Located on the arm · the subject is female · the patient indicates the lesion is raised or bumpy · Fitzpatrick phototype IV · a close-up photograph · the patient described the issue as a rash · symptoms reported: pain, enlargement, bothersome appearance, darkening, itching and burning · present for one to three months · the patient also reports fever, fatigue and joint pain — 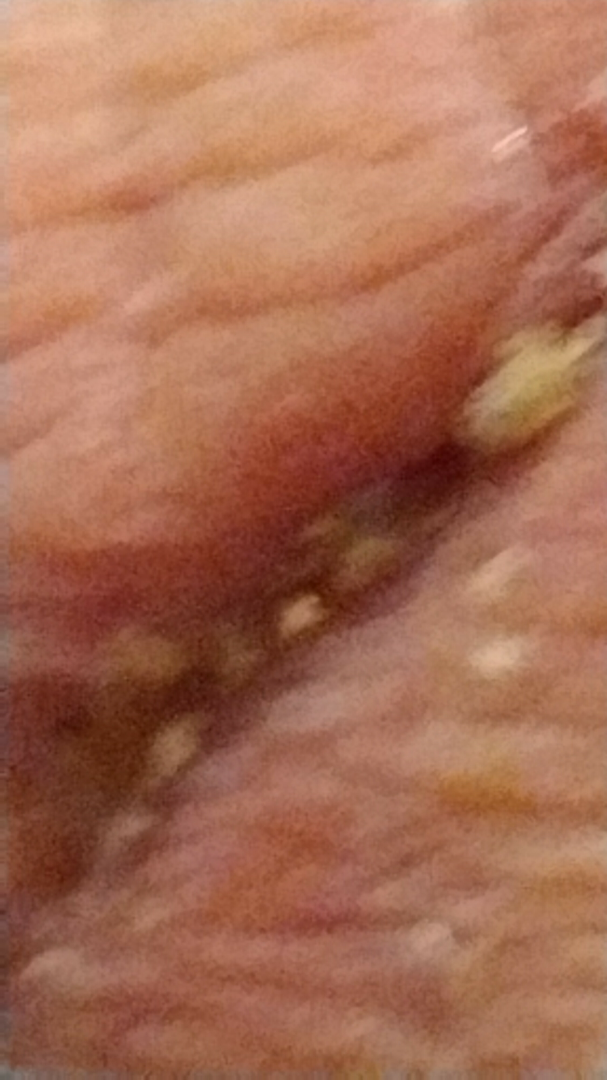Local infection of wound (leading).